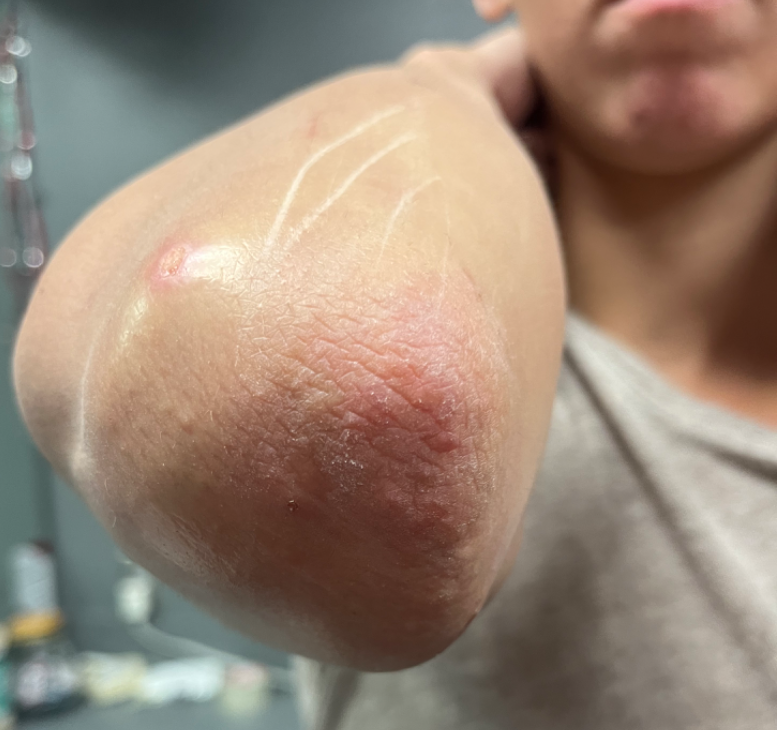clinical impression = the favored diagnosis is Psoriasis.